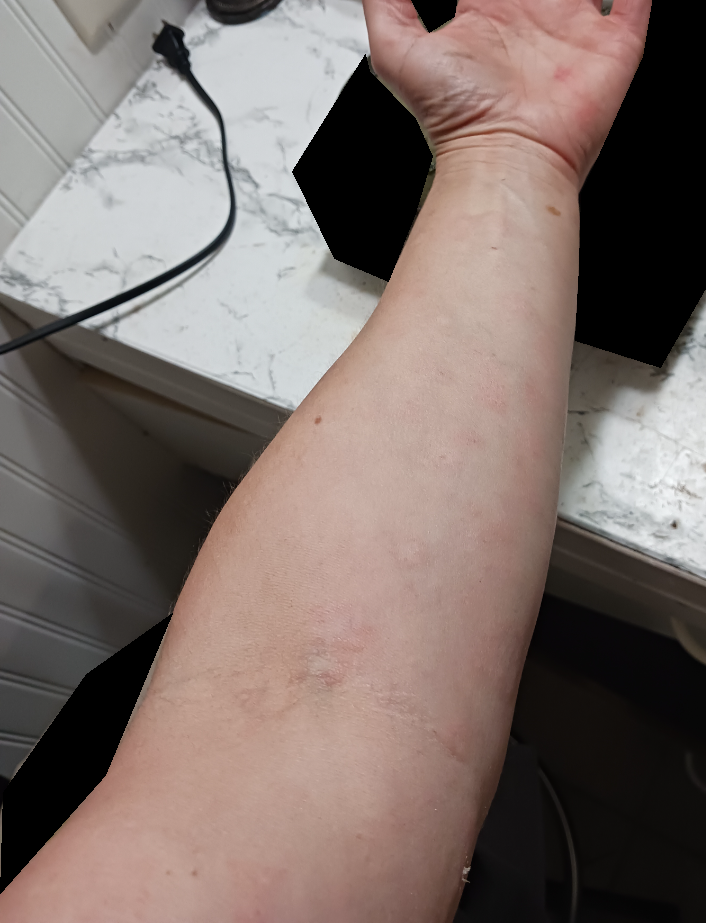The dermatologist could not determine a likely condition from the photograph alone.